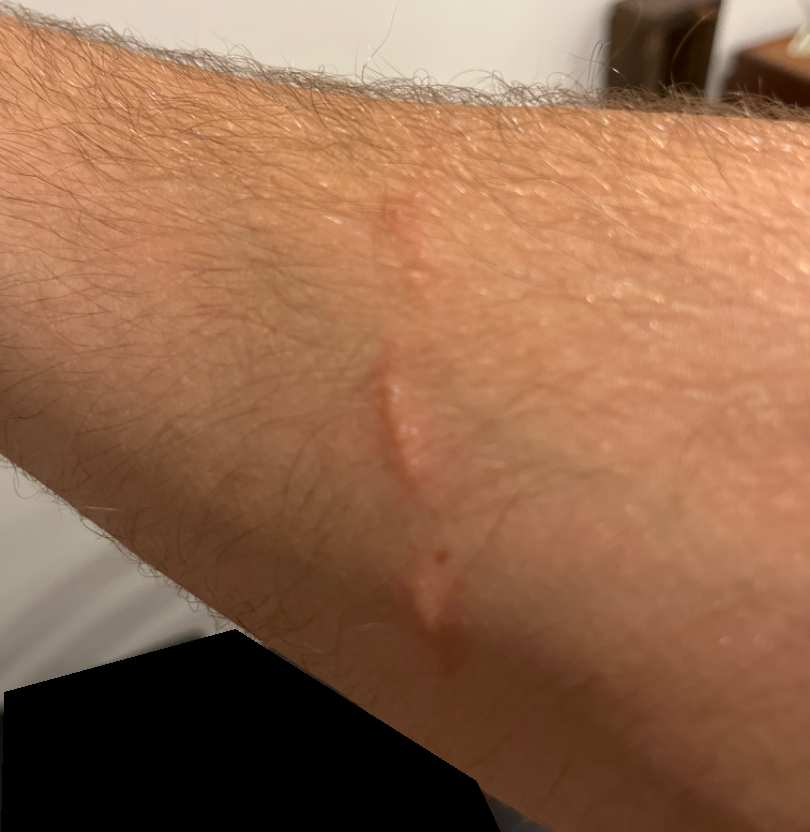Q: Could the case be diagnosed?
A: indeterminate
Q: Image view?
A: at an angle
Q: What is the affected area?
A: arm